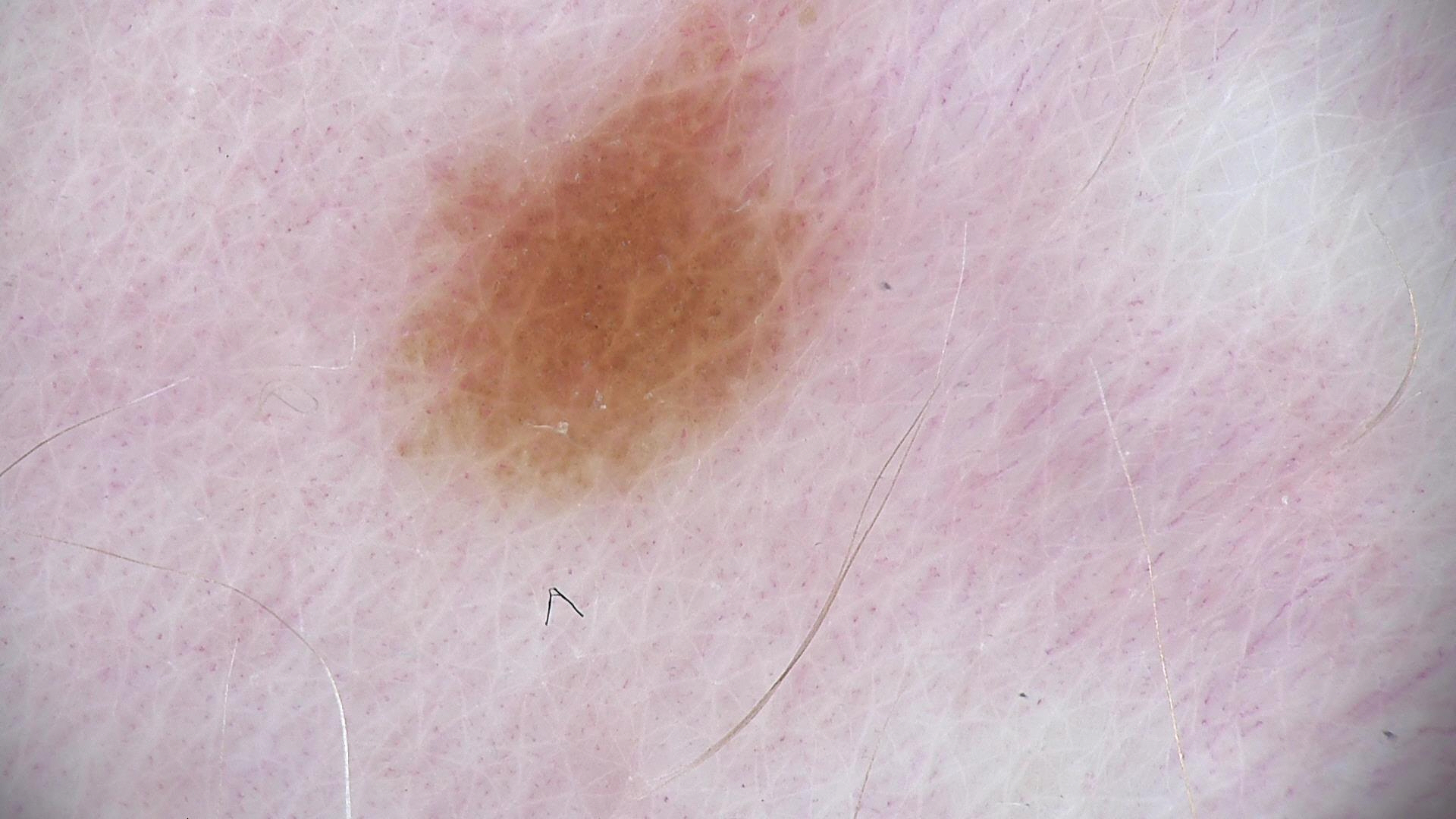Conclusion:
Diagnosed as a dysplastic junctional nevus.